The subject is 18–29, male. A close-up photograph — 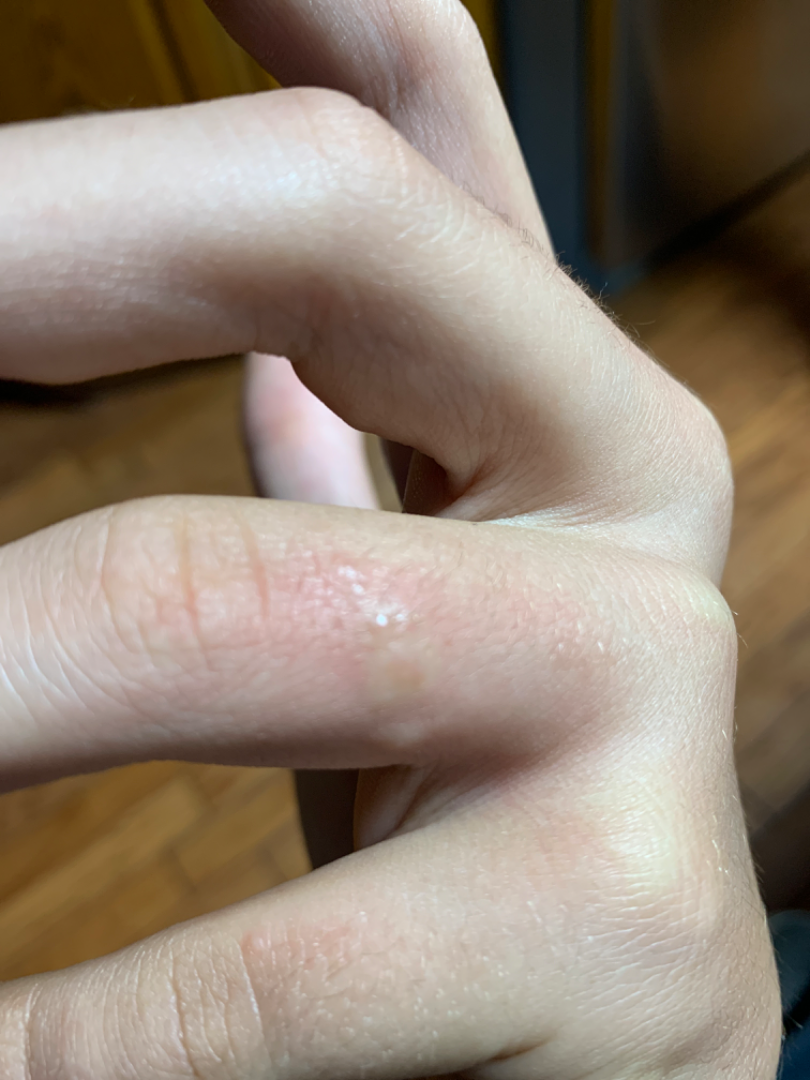The case was difficult to assess from the available photograph.
Reported duration is about one day.
Reported lesion symptoms include pain, itching and enlargement.
The contributor notes associated mouth sores.
Skin tone: lay reviewers estimated a MST of 1.
The lesion is described as fluid-filled.